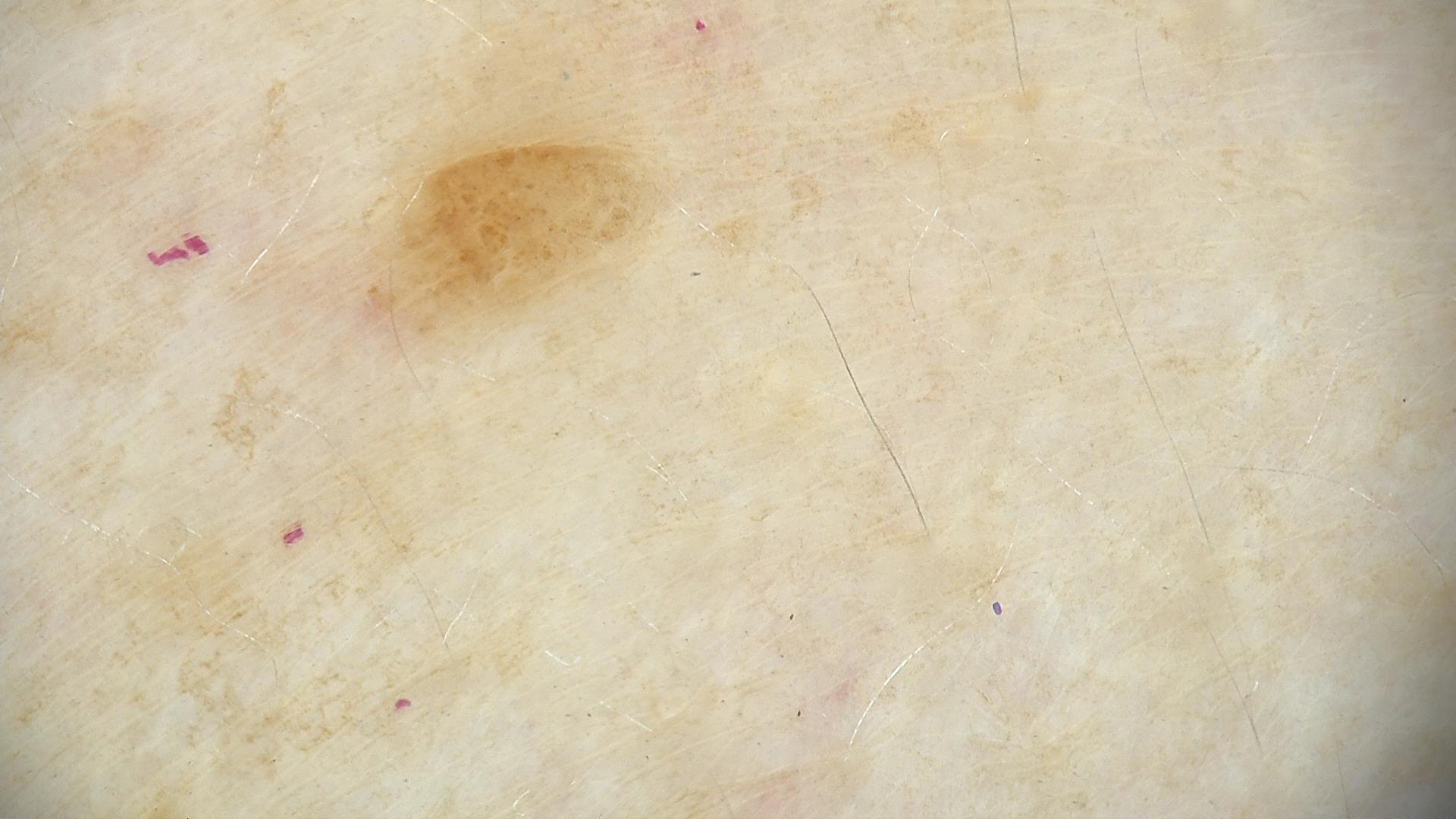A dermoscopic photograph of a skin lesion. The architecture is that of a banal lesion. Labeled as a compound nevus.